An image taken at a distance. The contributor is 30–39, female. Located on the leg and arm: 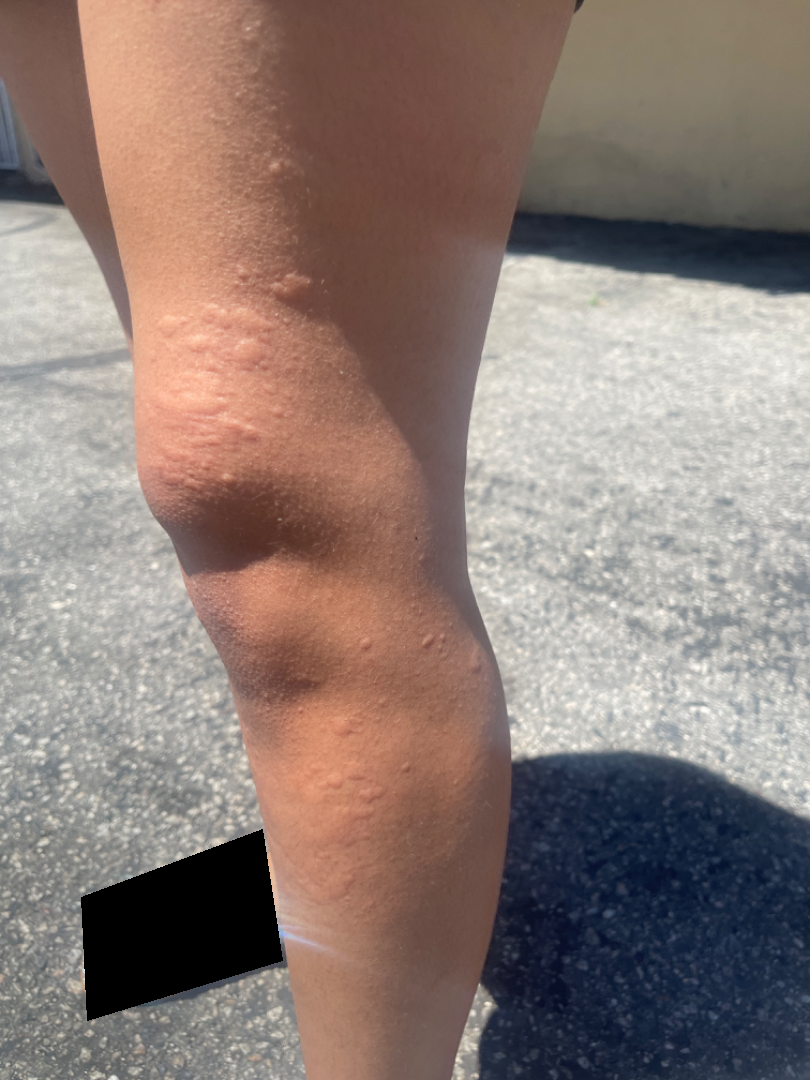On independent review by the dermatologists, Urticaria (primary).